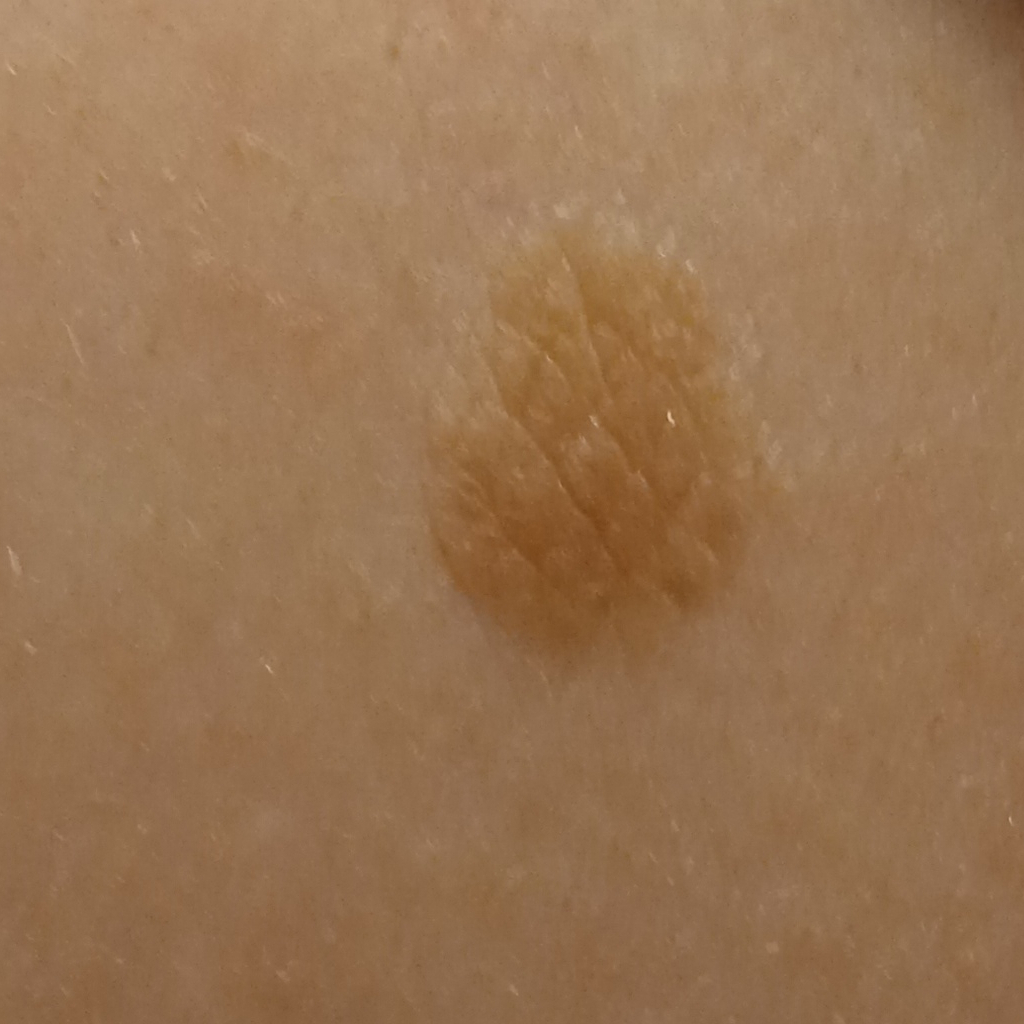Q: What was the diagnosis?
A: seborrheic keratosis (dermatologist consensus)